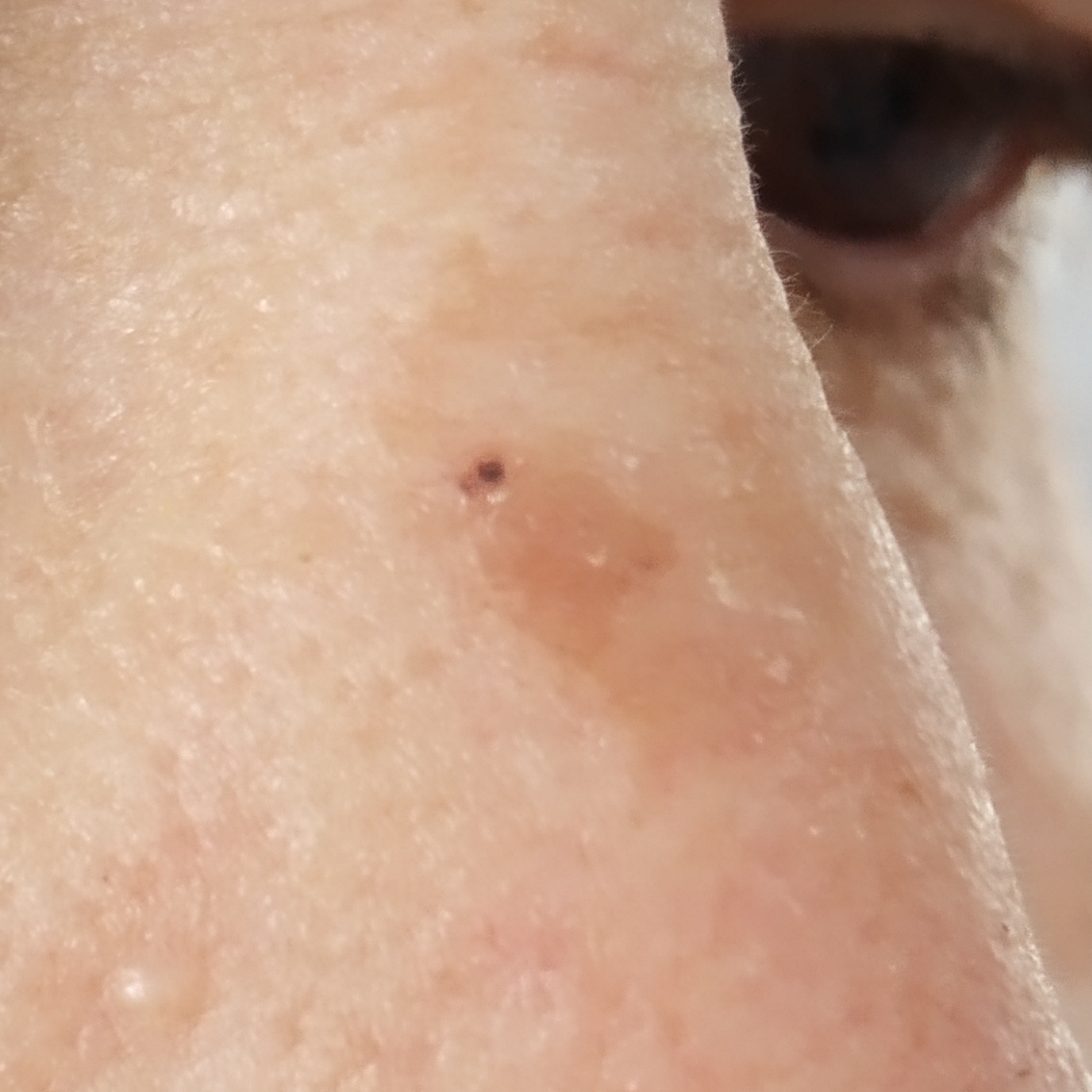Recorded as Fitzpatrick skin type III. A clinical photograph of a skin lesion. A female patient aged 57. The chart notes prior malignancy (patient or family). The lesion involves the nose. The lesion measures 2 × 1 mm. Per patient report, the lesion itches and has grown, but is not elevated. Histopathology confirmed a premalignant lesion — an actinic keratosis.